The subject is a male aged 58 to 62. Dermoscopy of a skin lesion: 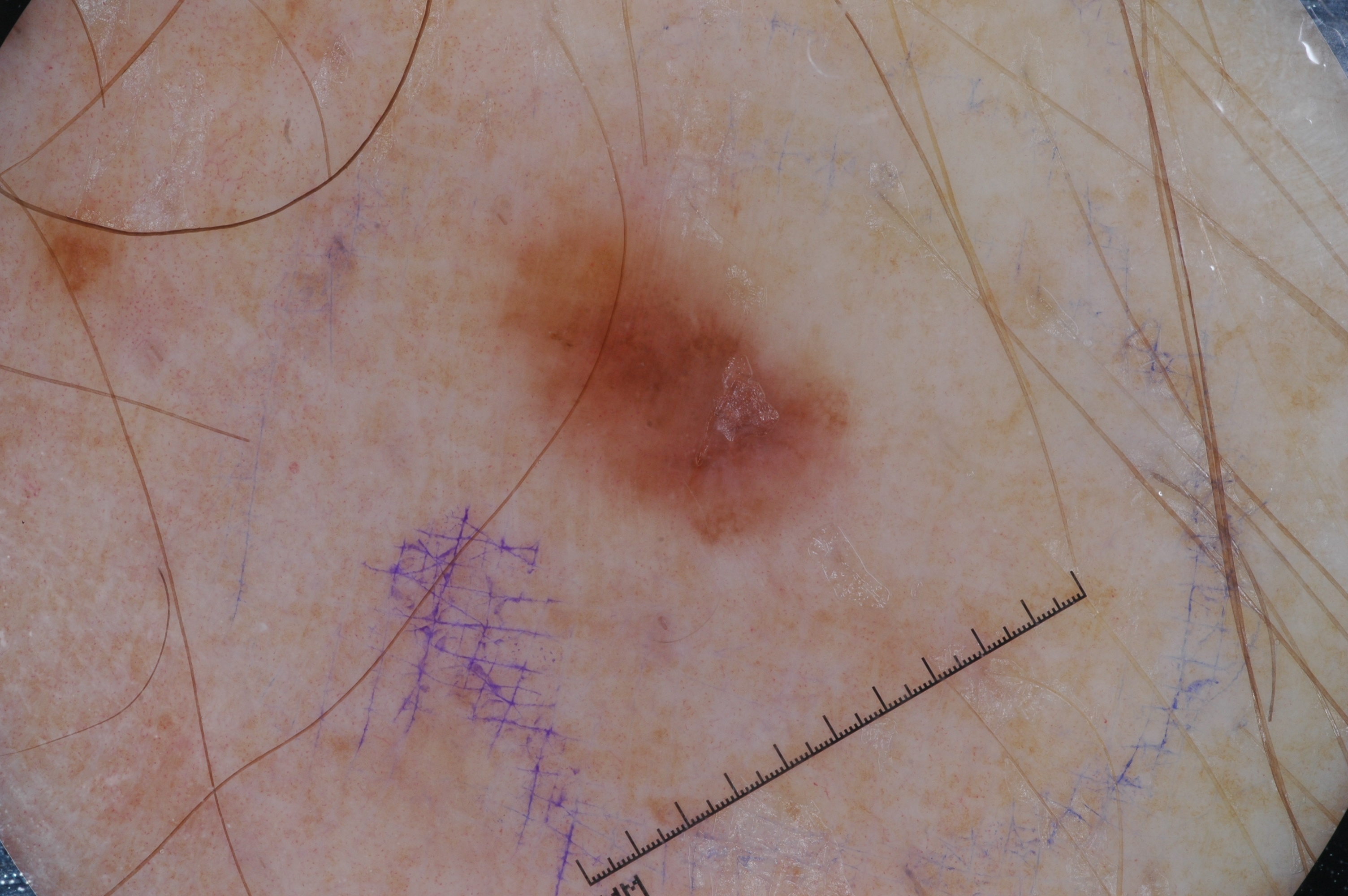Summary: A small lesion occupying a minor part of the field. With coordinates (x1, y1, x2, y2), lesion location: (485, 203, 853, 539). Dermoscopically, the lesion shows pigment network. Conclusion: Biopsy-confirmed as a melanoma, a malignant skin lesion.